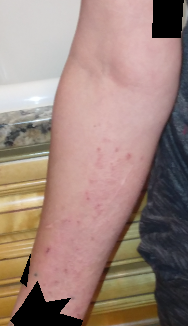subject = female, age 40–49 | systemic symptoms = joint pain | framing = at a distance | patient-reported symptoms = pain, itching and enlargement | anatomic site = arm | patient describes the issue as = a rash | lesion texture = raised or bumpy and rough or flaky | symptom duration = more than one year | impression = favoring Lichen Simplex Chronicus; also raised was Folliculitis; possibly Tinea; a remote consideration is Eczema.